The patient indicates the lesion is flat. The patient indicates the condition has been present for less than one week. The contributor is 18–29, male. The lesion is associated with itching and enlargement. The patient considered this a rash. The affected area is the top or side of the foot. A close-up photograph: 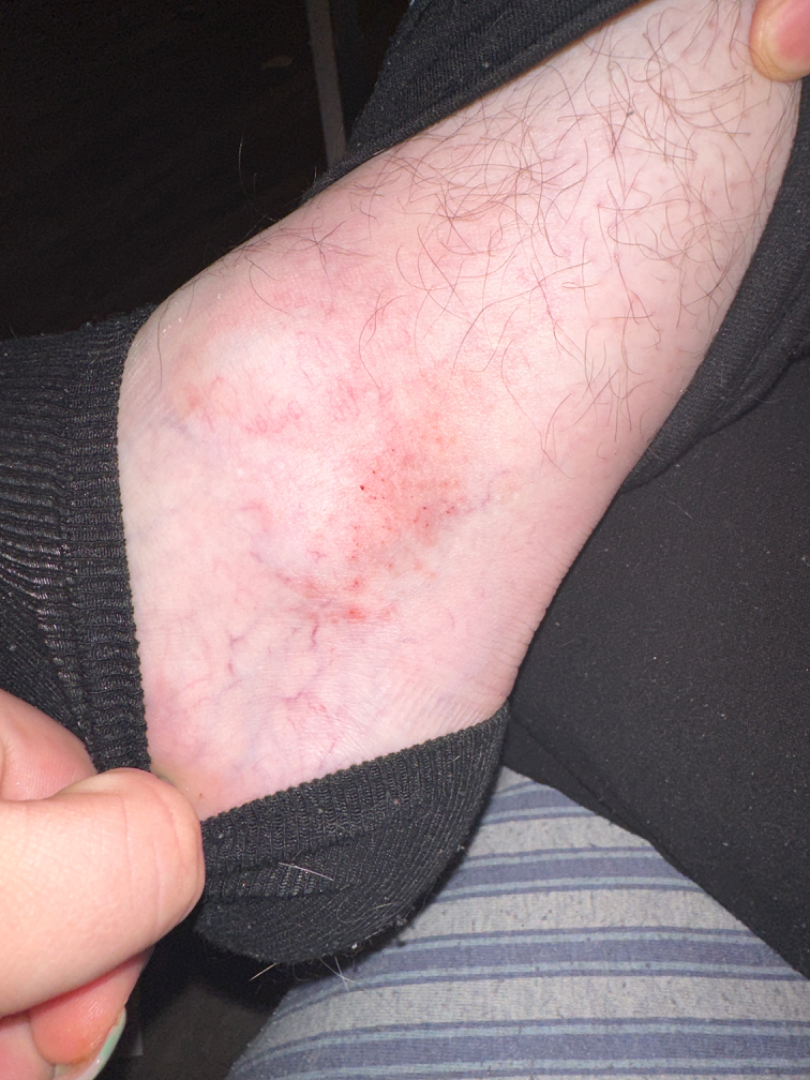Three independent reviewers: favoring Eczema; also consider Irritant Contact Dermatitis; lower on the differential is Stasis Dermatitis; a remote consideration is Allergic Contact Dermatitis.